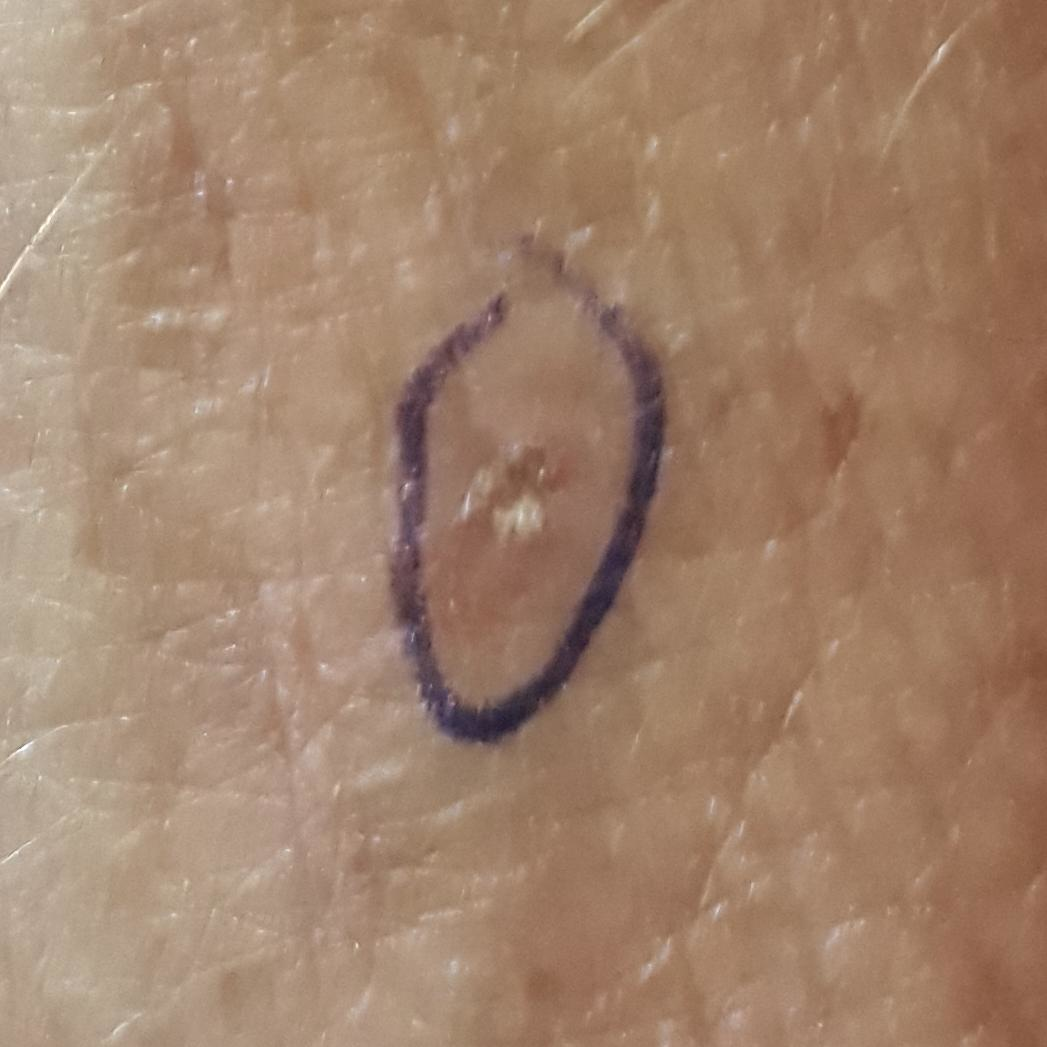  image: smartphone clinical photo
  patient:
    age: 33
  lesion_location: a hand
  symptoms:
    present:
      - growth
      - itching
      - elevation
    absent:
      - bleeding
  diagnosis:
    name: actinic keratosis
    code: ACK
    malignancy: indeterminate
    confirmation: clinical consensus